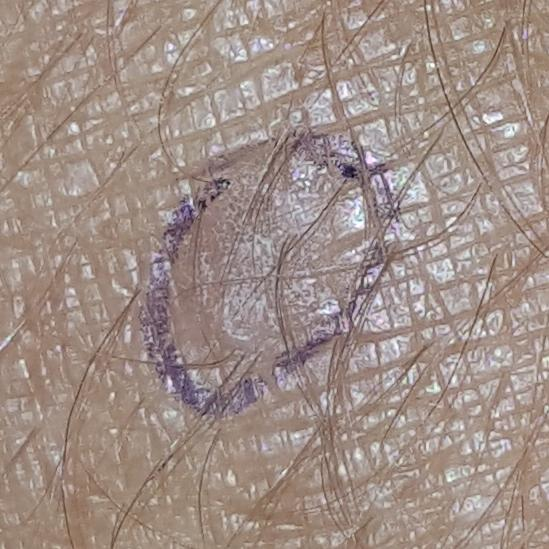A clinical photograph showing a skin lesion.
A subject 62 years of age.
Located on a forearm.
By the patient's account, the lesion itches and is elevated.
The consensus clinical diagnosis was a seborrheic keratosis.